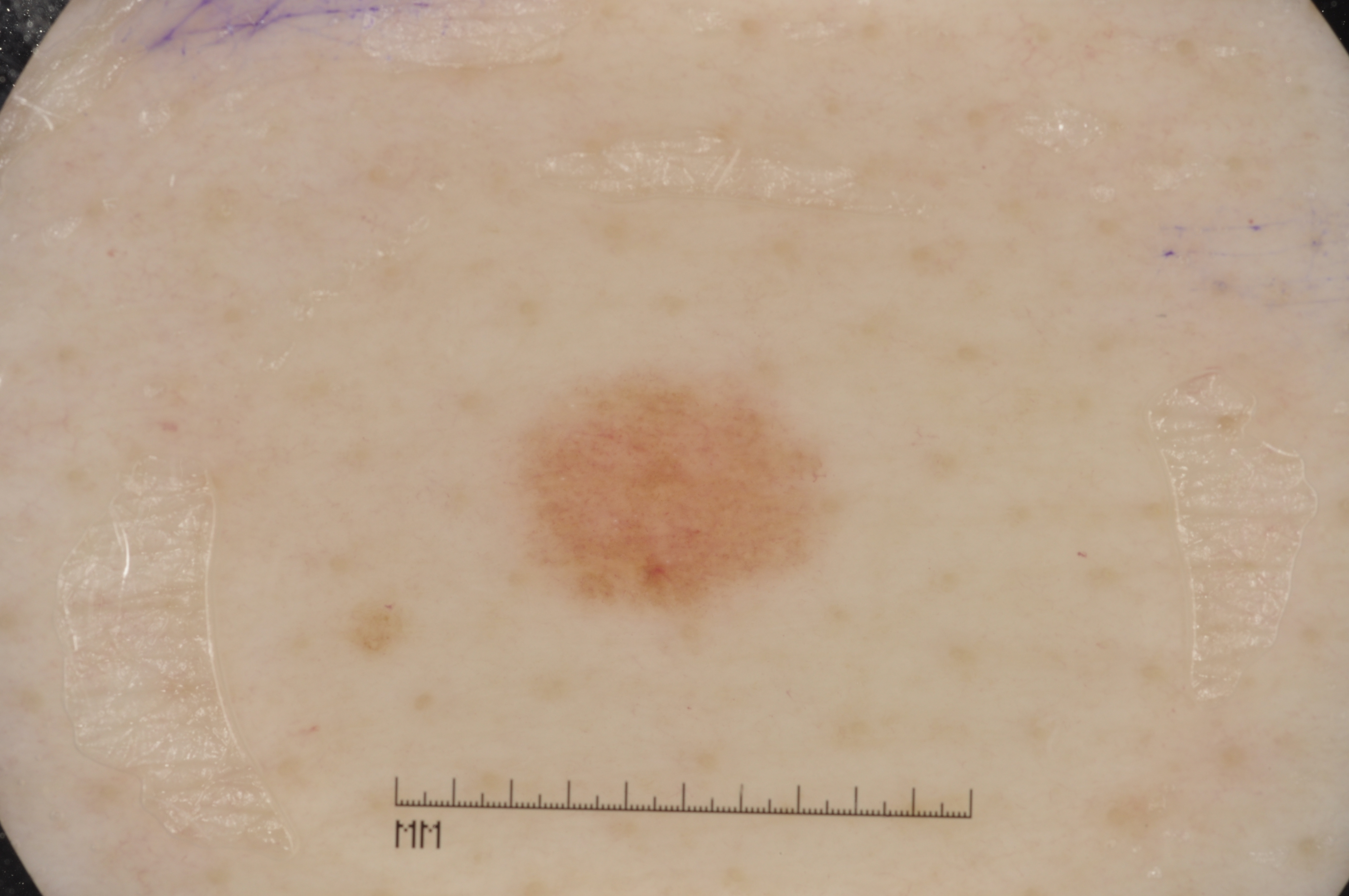A dermoscopic image of a skin lesion.
The subject is a female about 55 years old.
The dermoscopic pattern shows milia-like cysts, with no pigment network, negative network, or streaks.
In (x1, y1, x2, y2) order, the lesion's extent is 517, 378, 822, 616.
The lesion occupies roughly 5% of the field.
The clinical diagnosis was a melanocytic nevus, a benign lesion.